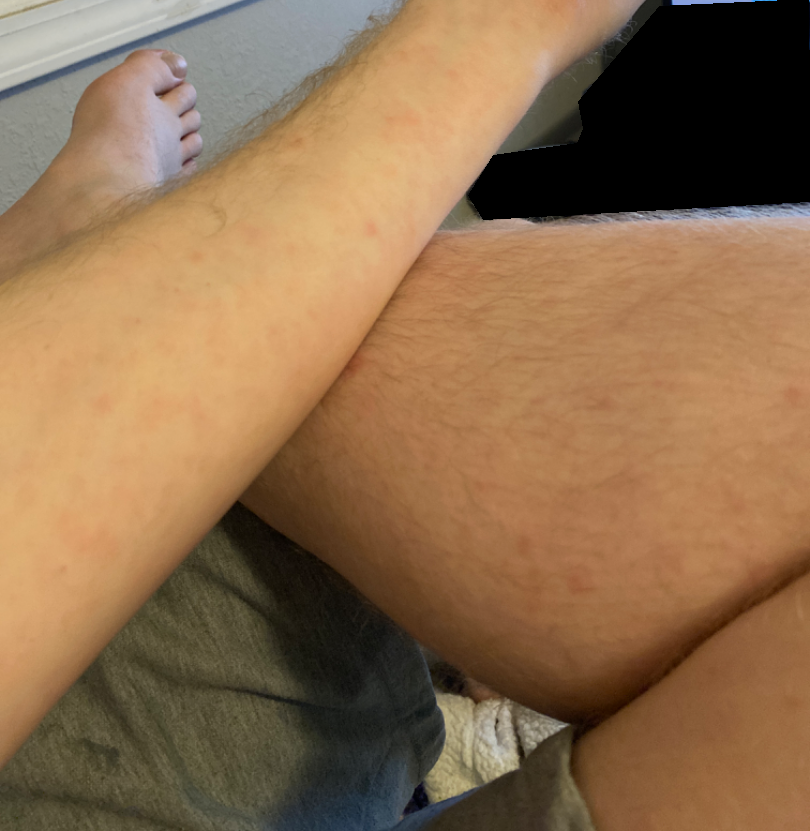Findings:
* assessment: indeterminate from the photograph
* view: at an angle
* lesion symptoms: bothersome appearance
* symptom duration: one to four weeks
* affected area: front of the torso, leg, back of the torso and arm